A skin lesion imaged with a dermatoscope.
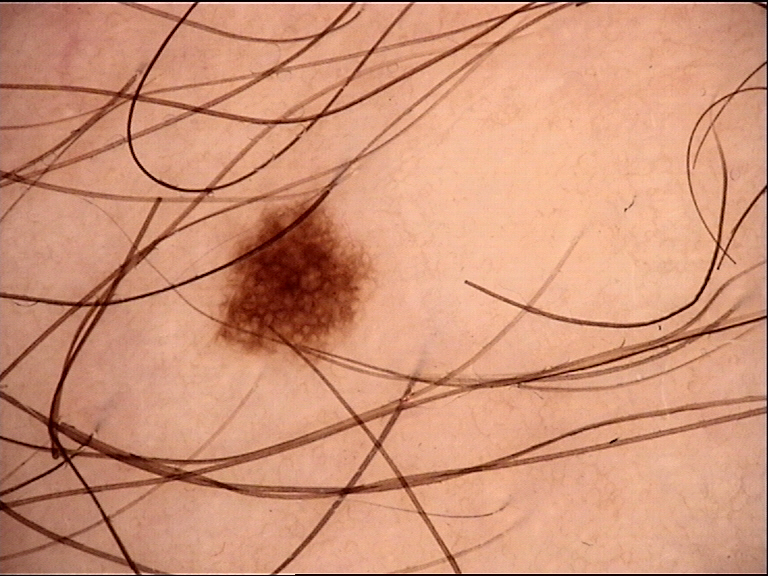The diagnosis was a dysplastic junctional nevus.